The lesion is described as rough or flaky, fluid-filled and raised or bumpy · a close-up photograph · the condition has been present for one to four weeks · self-categorized by the patient as a rash · reported lesion symptoms include burning, bothersome appearance, itching, bleeding, enlargement, pain and darkening · the patient also reports joint pain · the arm, palm, back of the hand and head or neck are involved.
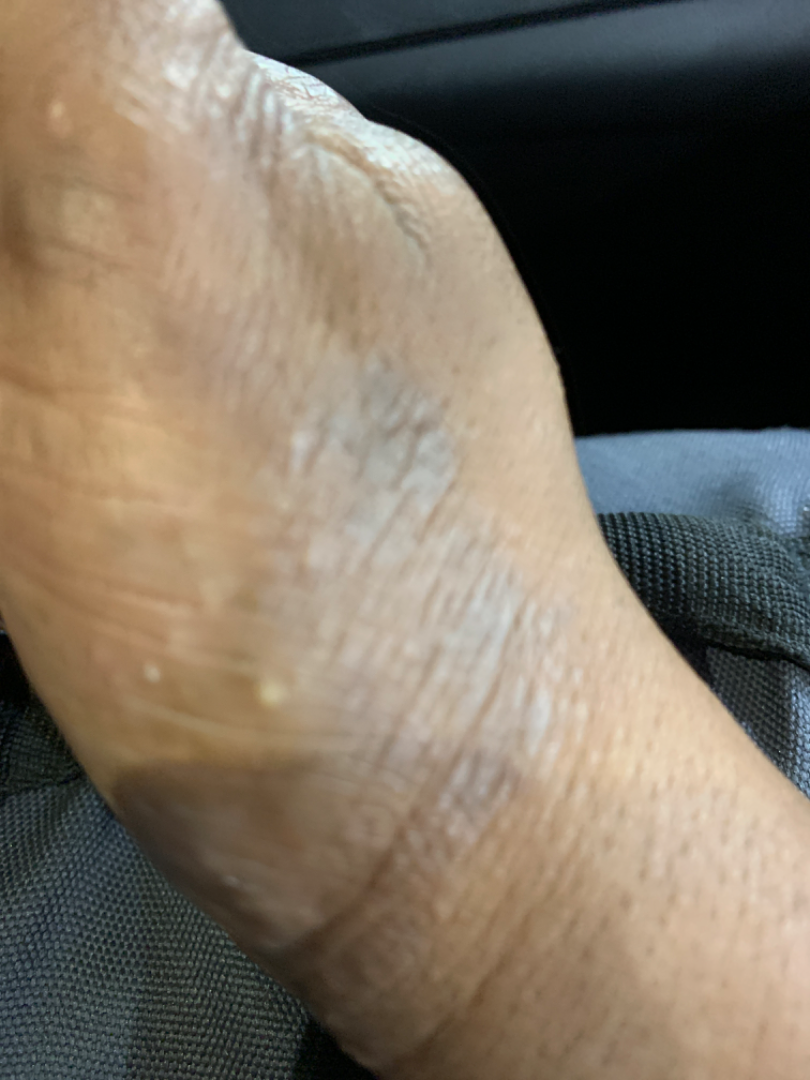The reviewer was unable to grade this case for skin condition.